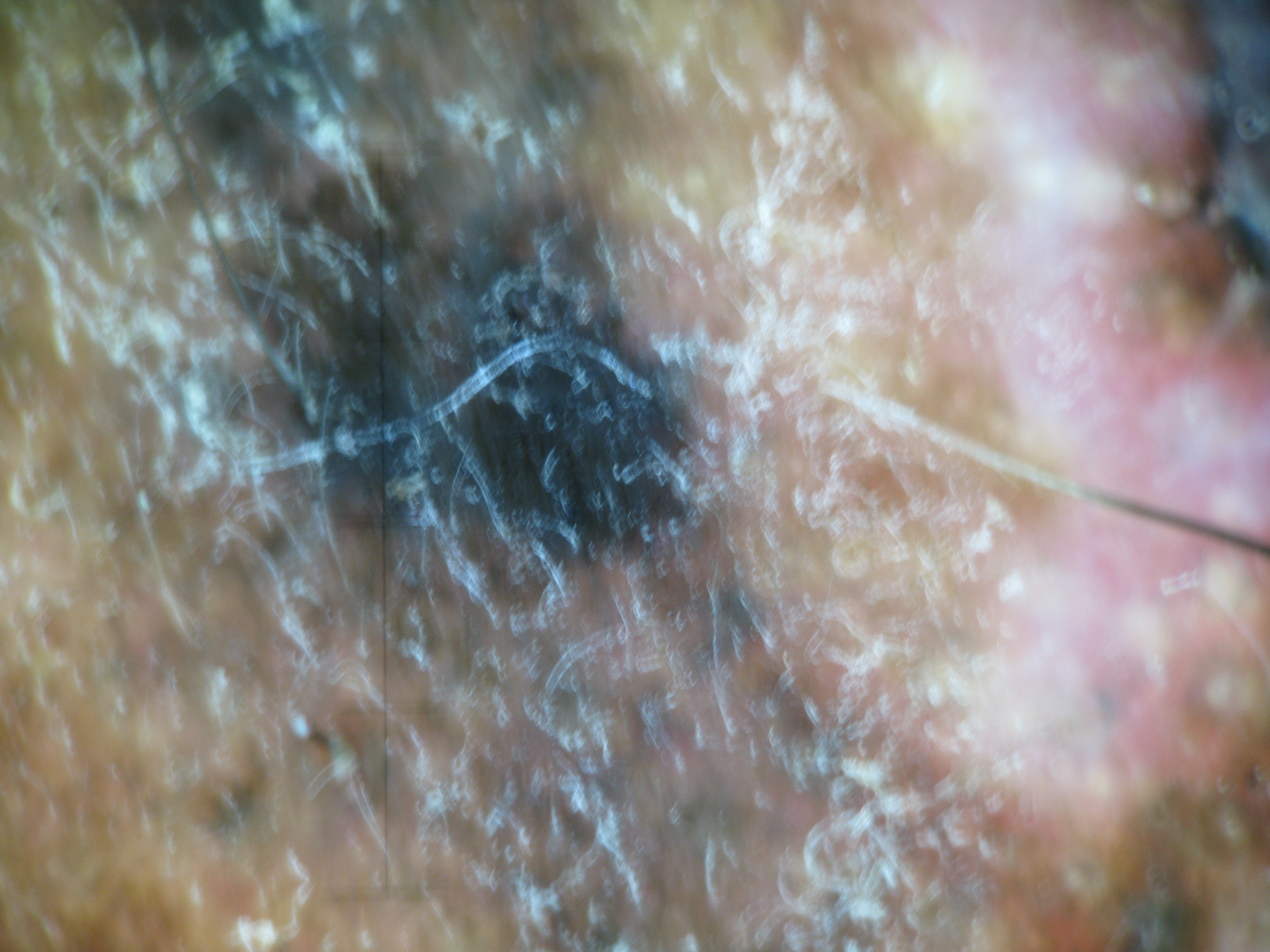Biopsy-confirmed as a lentigo maligna melanoma.